The photograph was taken at an angle.
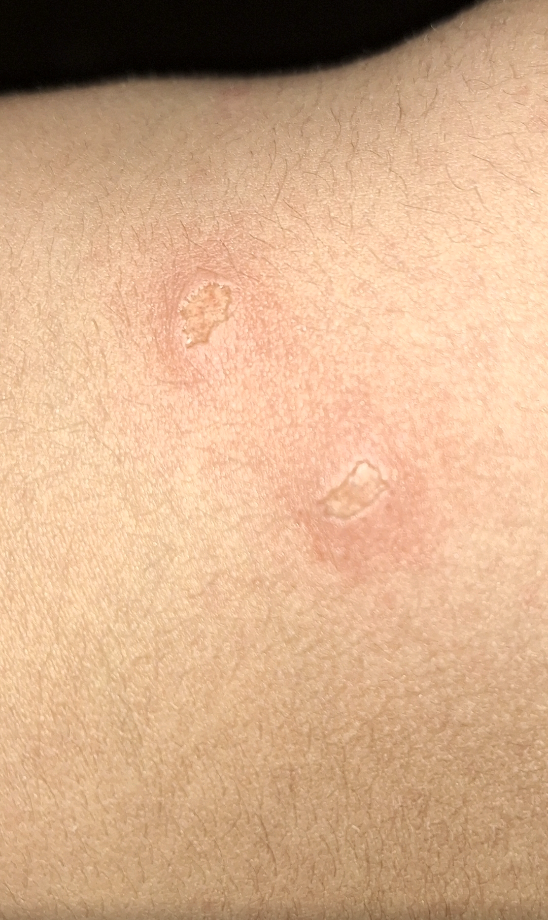assessment = indeterminate from the photograph